An image taken at an angle.
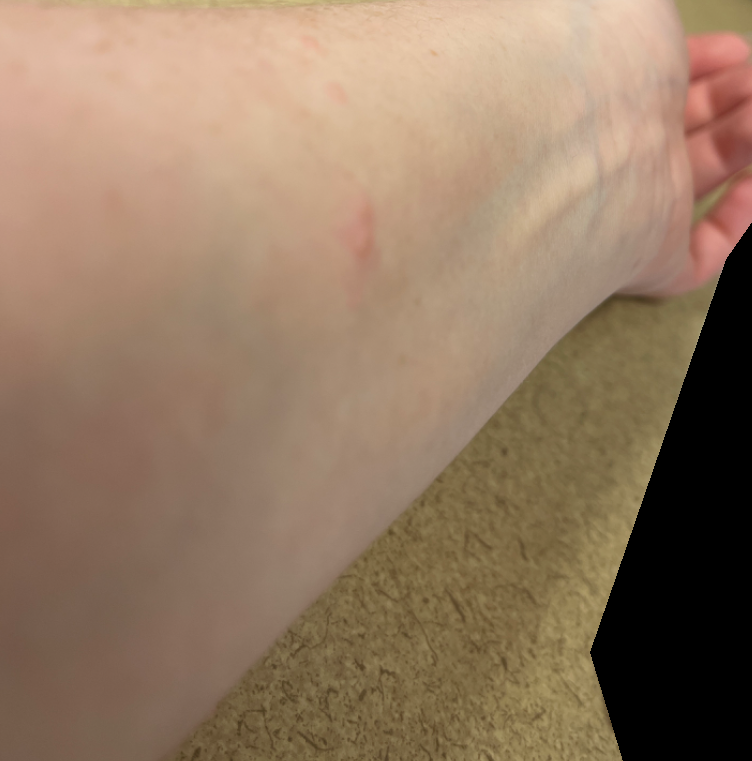<summary>
<assessment>ungradable on photographic review</assessment>
</summary>